The patient describes having a moderate number of moles; the patient says their skin tans without first burning; referred with a clinical suspicion of seborrheic keratosis; by self-report, a personal history of cancer and a family history of skin cancer; a clinical photograph of a skin lesion; a female subject 64 years of age:
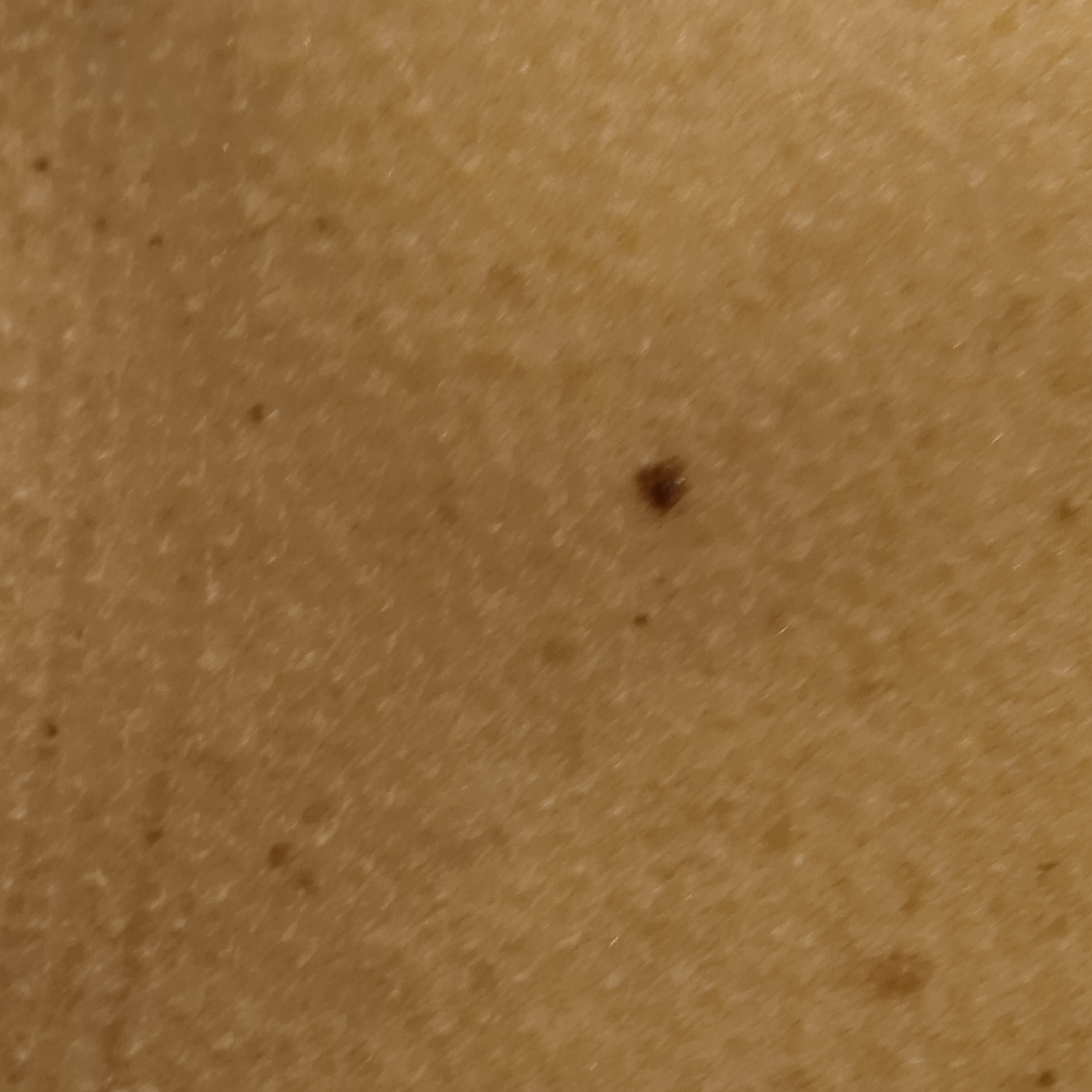{"lesion_location": "the back", "lesion_size": {"diameter_mm": 3.5}, "diagnosis": {"name": "seborrheic keratosis", "malignancy": "benign", "procedure": "excision"}}